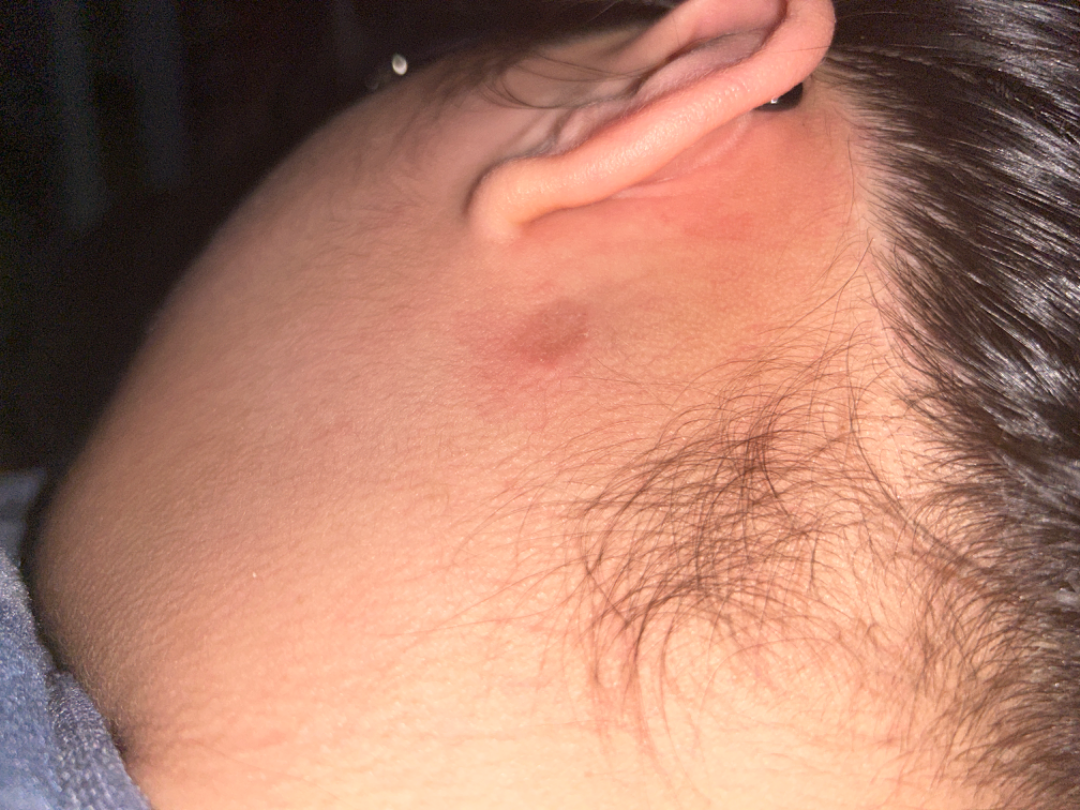| feature | finding |
|---|---|
| assessment | not assessable |
| associated systemic symptoms | none reported |
| location | head or neck |
| lesion symptoms | itching and bothersome appearance |
| texture | raised or bumpy, flat and rough or flaky |
| duration | less than one week |
| skin tone | Fitzpatrick skin type IV |
| photo taken | at an angle |